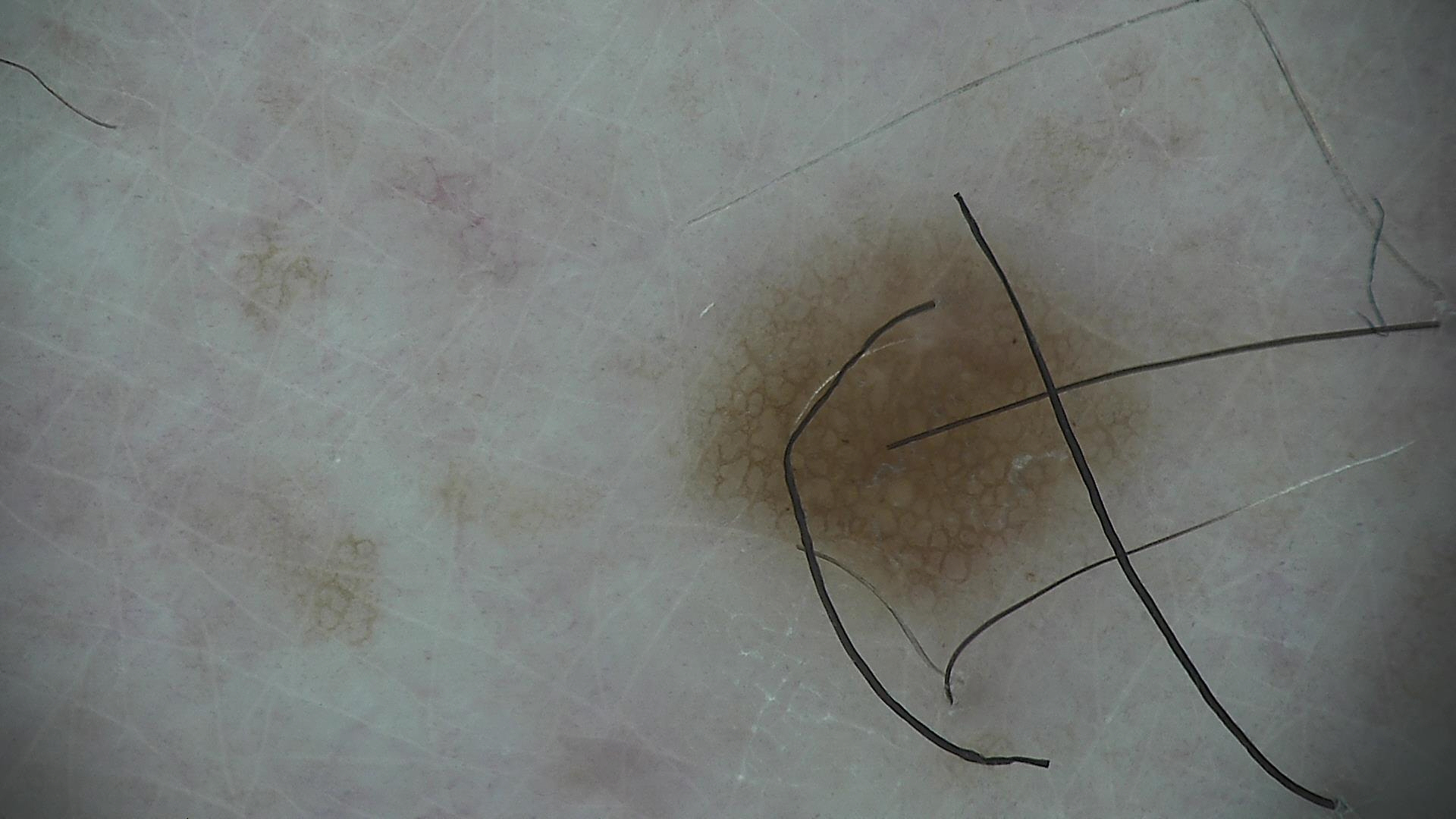Findings:
• image type · dermoscopy
• diagnostic label · dysplastic junctional nevus (expert consensus)